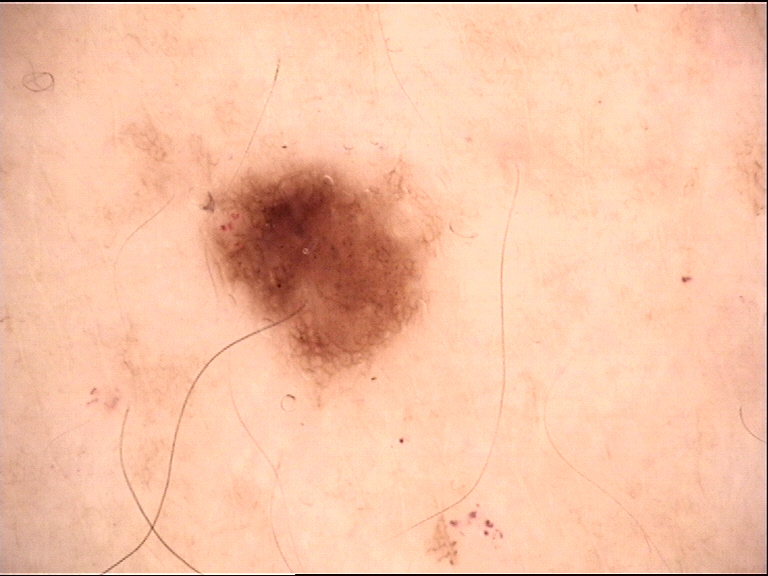A dermoscopic photograph of a skin lesion.
The diagnosis was a benign lesion — a dysplastic junctional nevus.